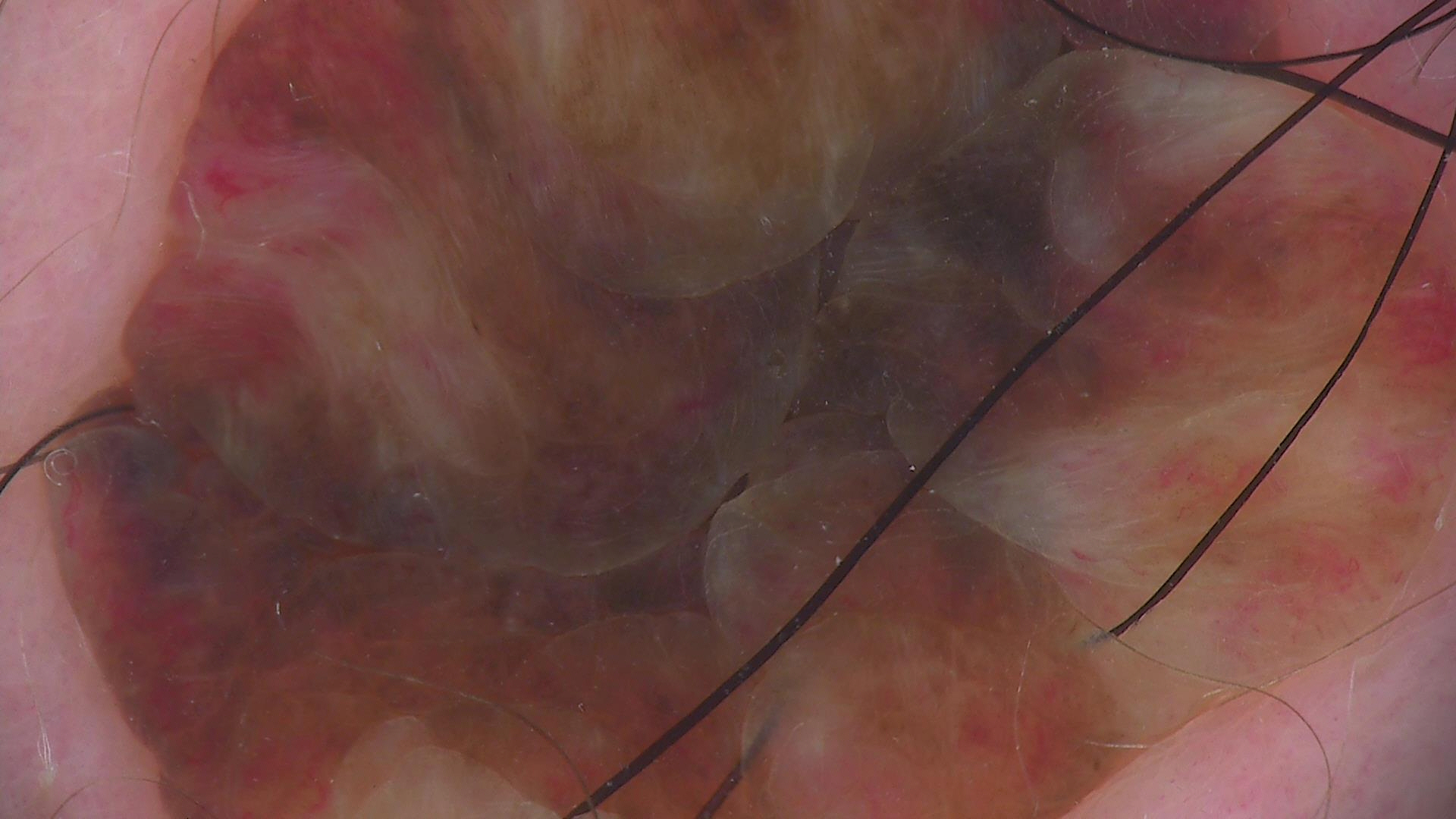Summary:
Dermoscopy of a skin lesion. The architecture is that of a banal lesion.
Impression:
The diagnosis was a dermal nevus.